The photo was captured at an angle; the leg is involved — 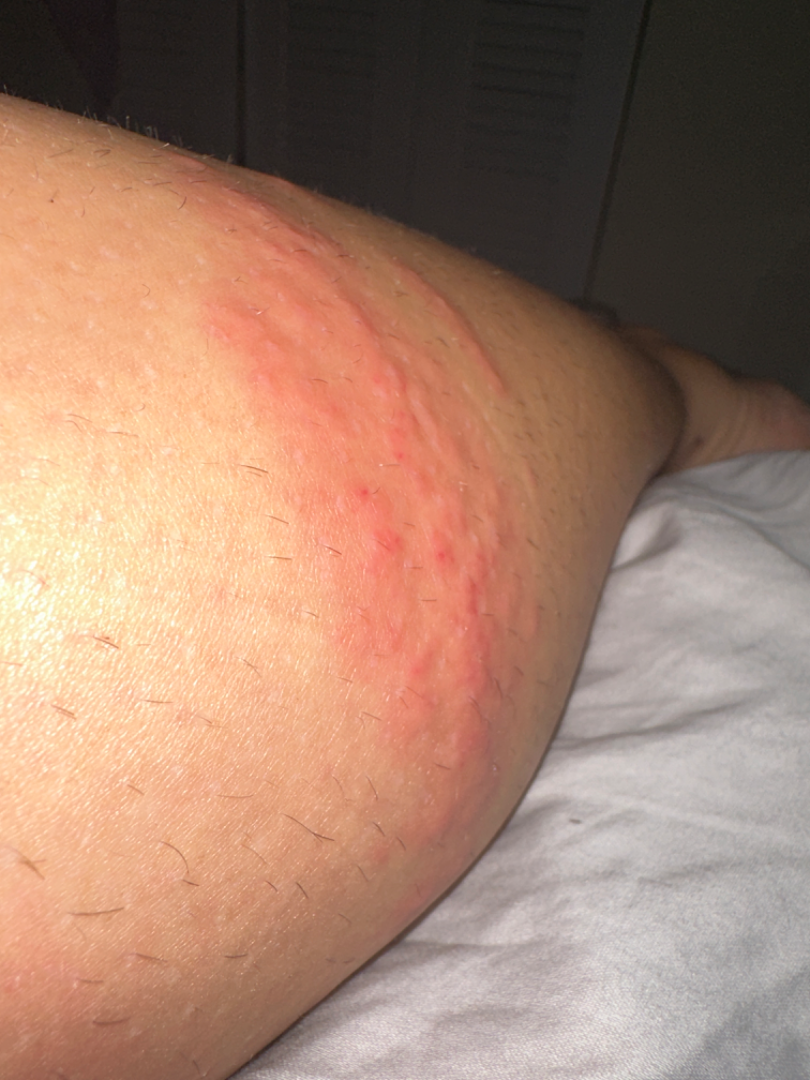Findings: The case was indeterminate on photographic review.